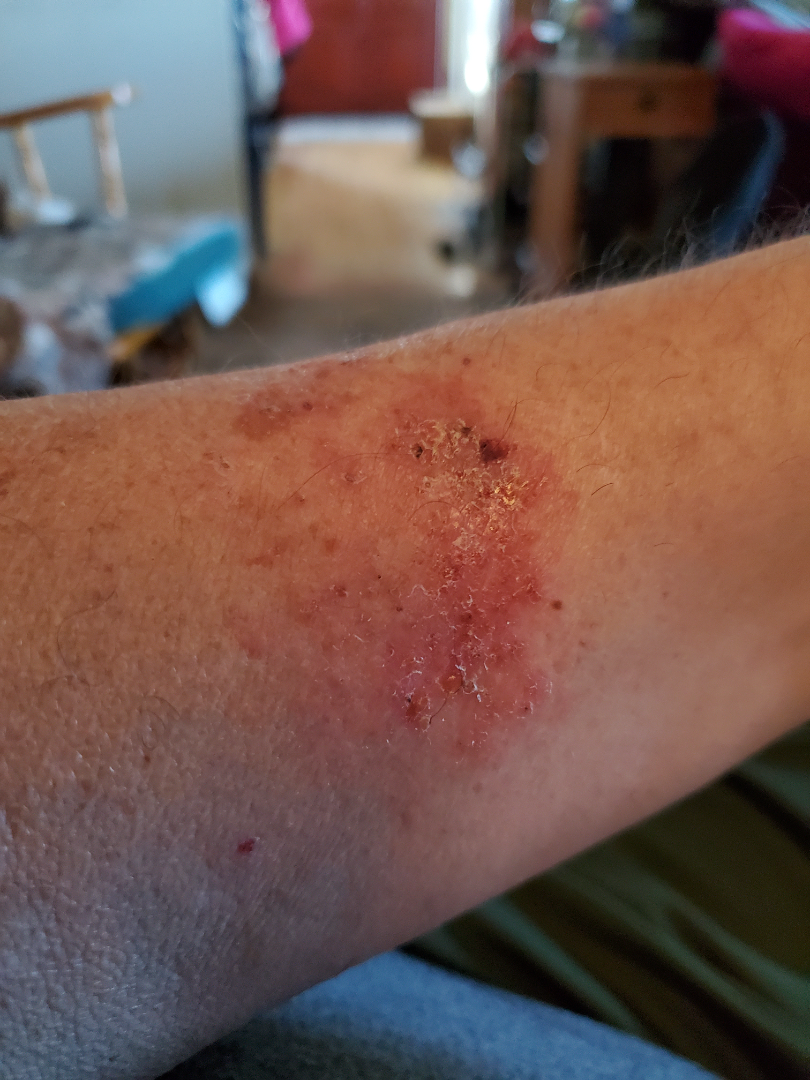shot_type: close-up
texture: fluid-filled
duration: one to four weeks
differential:
  tied_lead:
    - Tinea
    - Eczema
  unlikely:
    - Psoriasis